Texture is reported as fluid-filled and raised or bumpy; reported duration is one to four weeks; this image was taken at an angle; the lesion involves the arm — 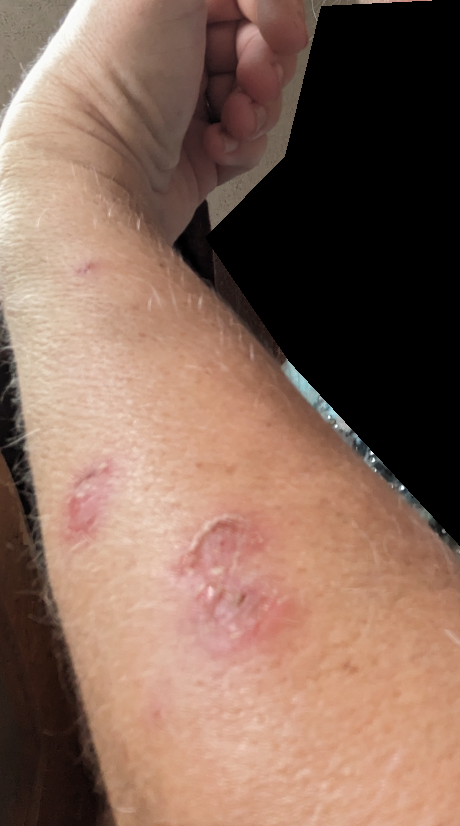{"differential": {"leading": ["Lichen Simplex Chronicus"], "considered": ["Skin infection"]}}